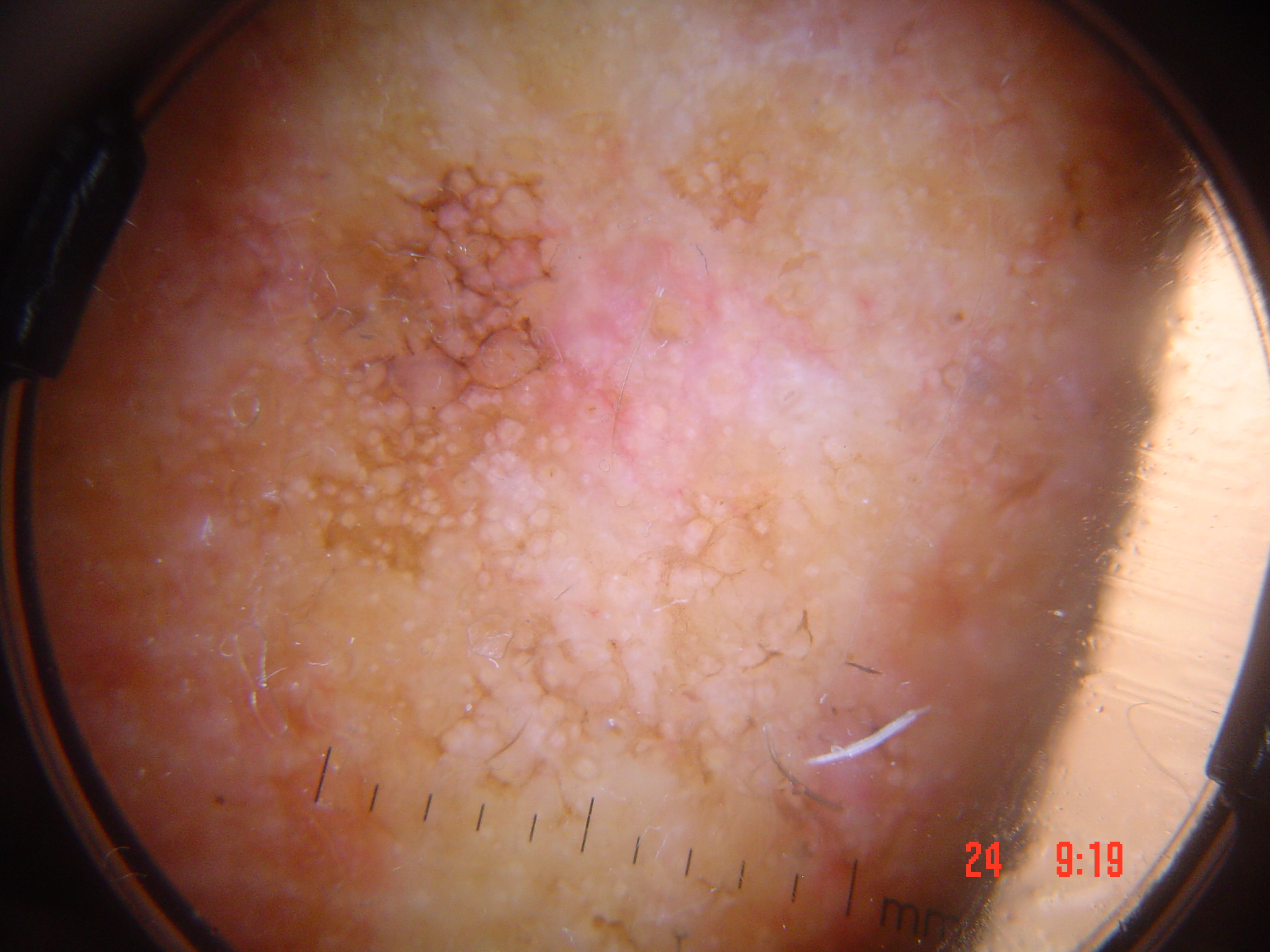Impression: Consistent with a keratinocytic lesion — an actinic keratosis.